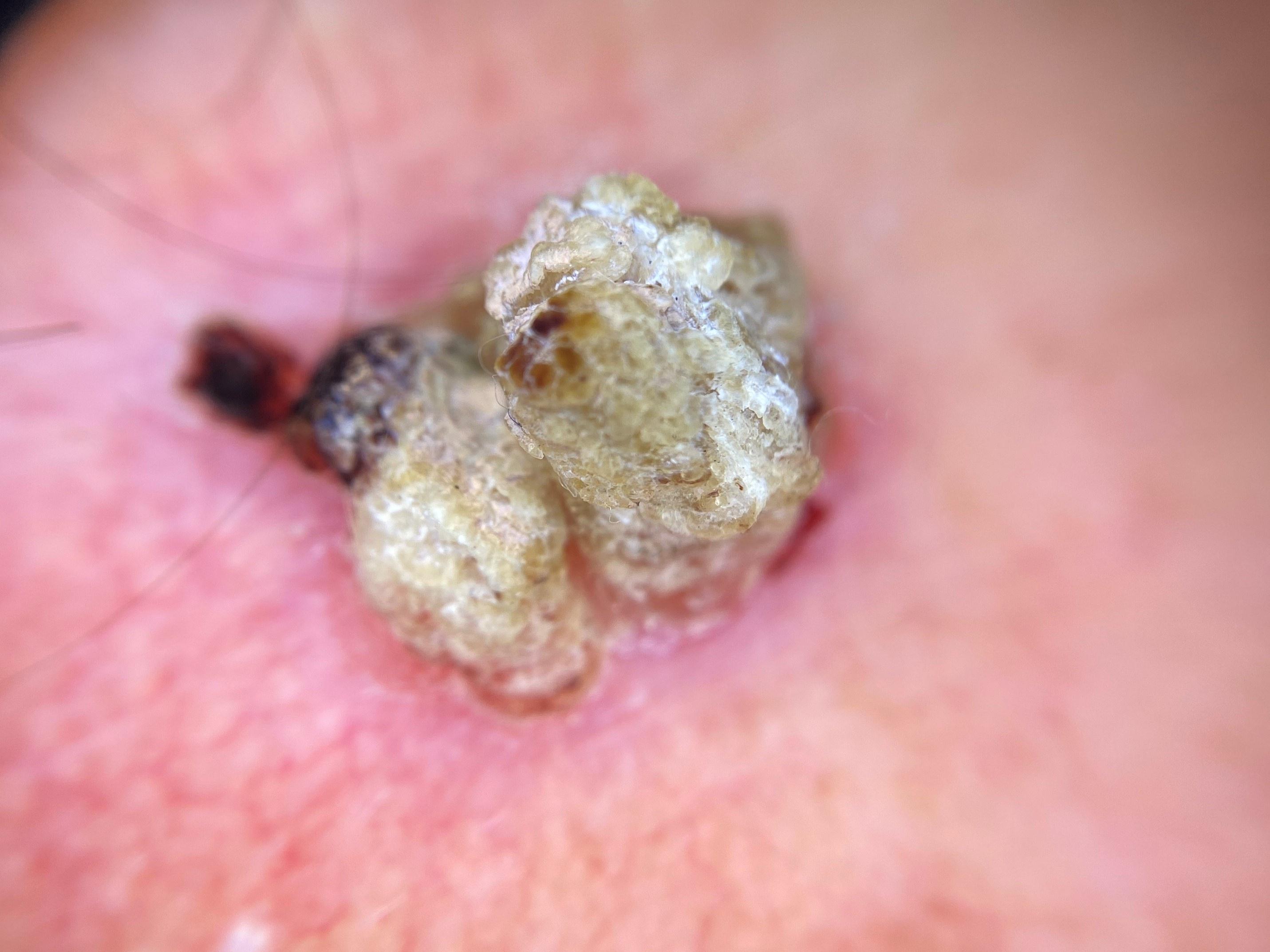Q: What is the diagnosis?
A: Squamous cell carcinoma (biopsy-proven)